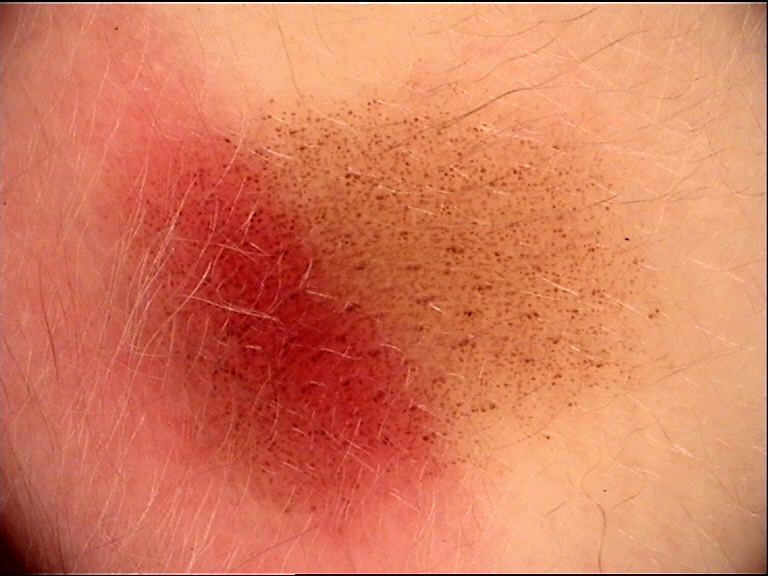Dermoscopy of a skin lesion.
The diagnosis was a banal lesion — a congenital junctional nevus.